The chart notes pesticide exposure and prior malignancy (patient or family). A clinical photograph of a skin lesion. The patient was assessed as Fitzpatrick II — 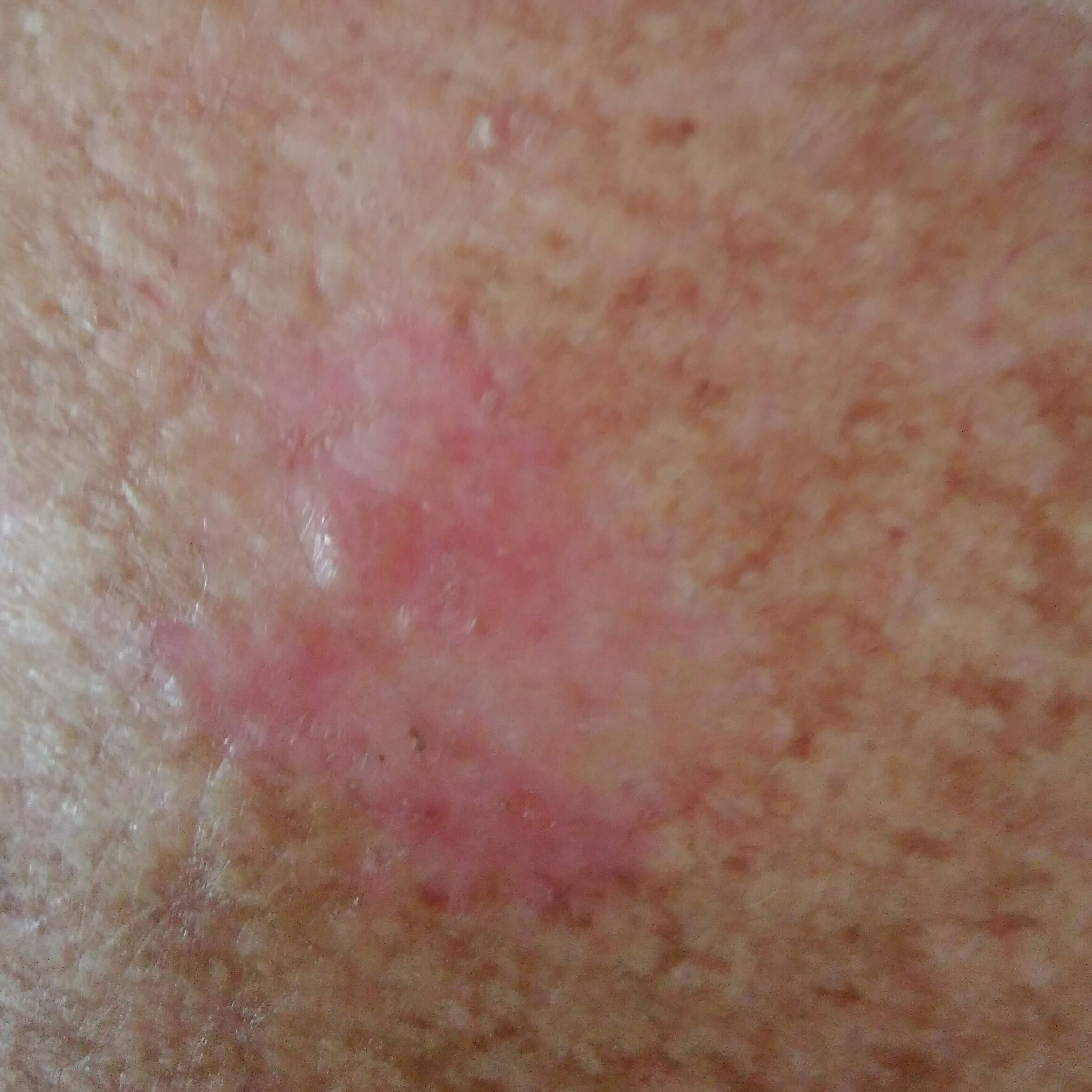The lesion is roughly 21 by 20 mm.
The patient describes that the lesion itches.
Biopsy-confirmed as a basal cell carcinoma.